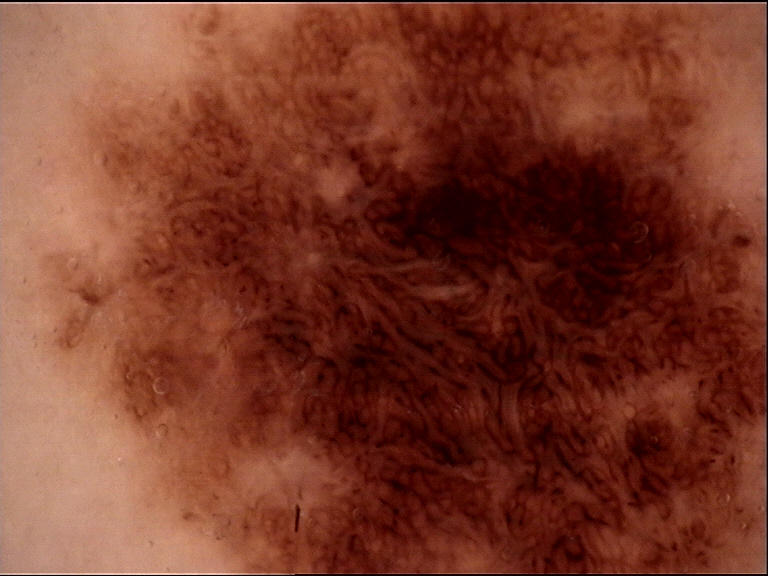  diagnosis:
    name: dysplastic junctional nevus
    code: jd
    malignancy: benign
    super_class: melanocytic
    confirmation: expert consensus